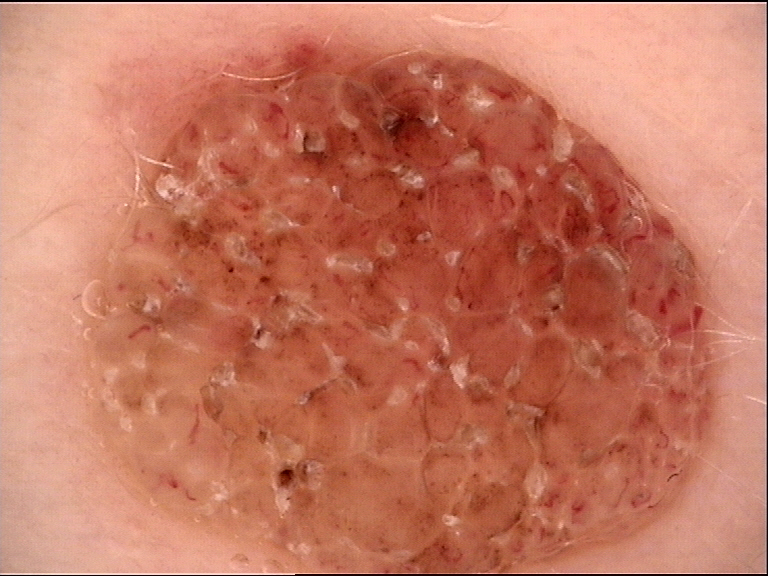Dermoscopy of a skin lesion. The architecture is that of a banal lesion. Diagnosed as a dermal nevus.